A male subject approximately 85 years of age or older · recorded as FST II · contact-polarized dermoscopy of a skin lesion.
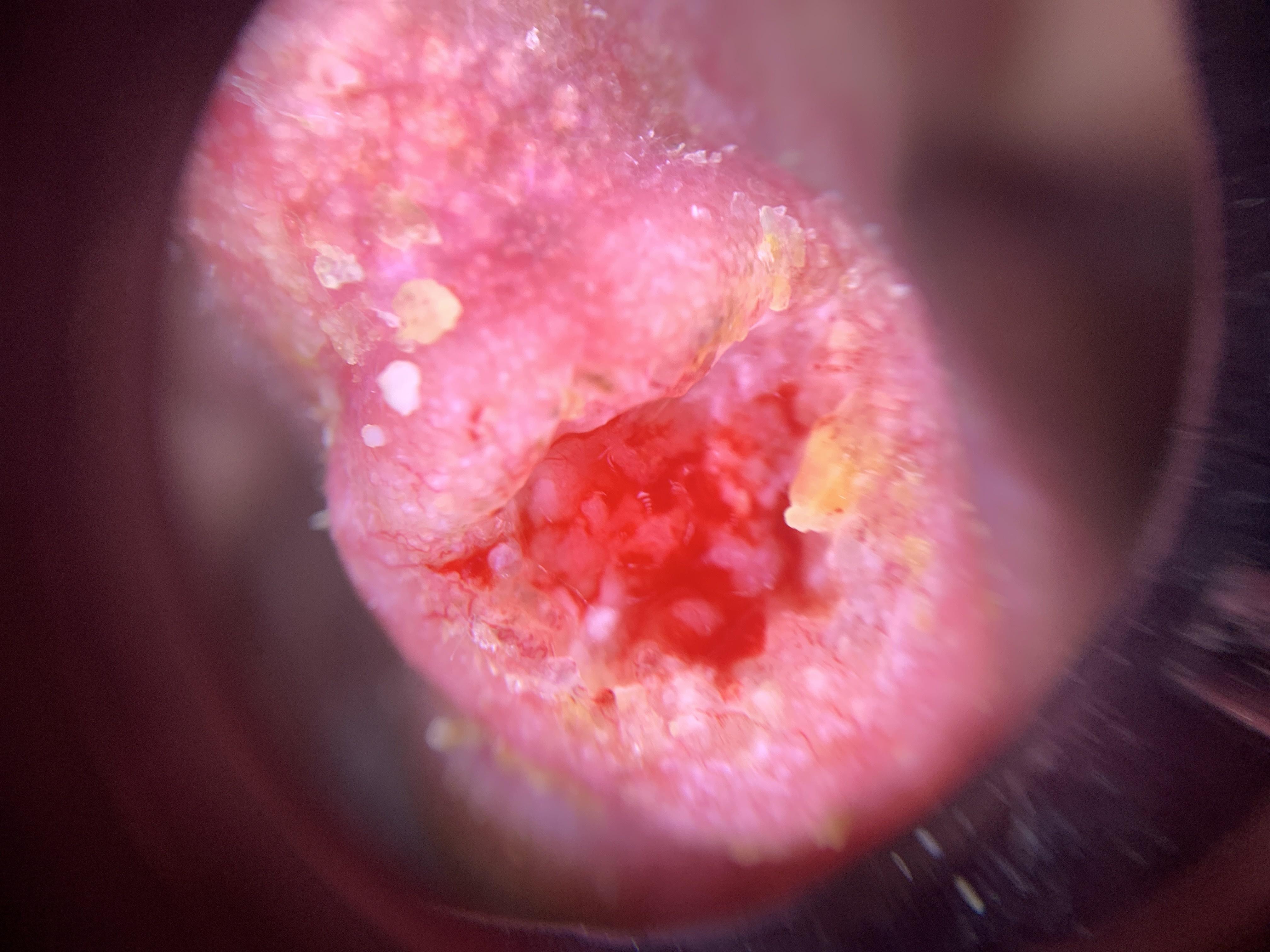Findings:
The lesion involves the head or neck.
Diagnosis:
Histopathology confirmed a lesion of epidermal origin — a squamous cell carcinoma.